The contributor reports the lesion is flat · close-up view · reported lesion symptoms include bothersome appearance · no relevant systemic symptoms · the contributor reports the condition has been present for one to three months · the affected area is the top or side of the foot and leg · the patient is 18–29, male — 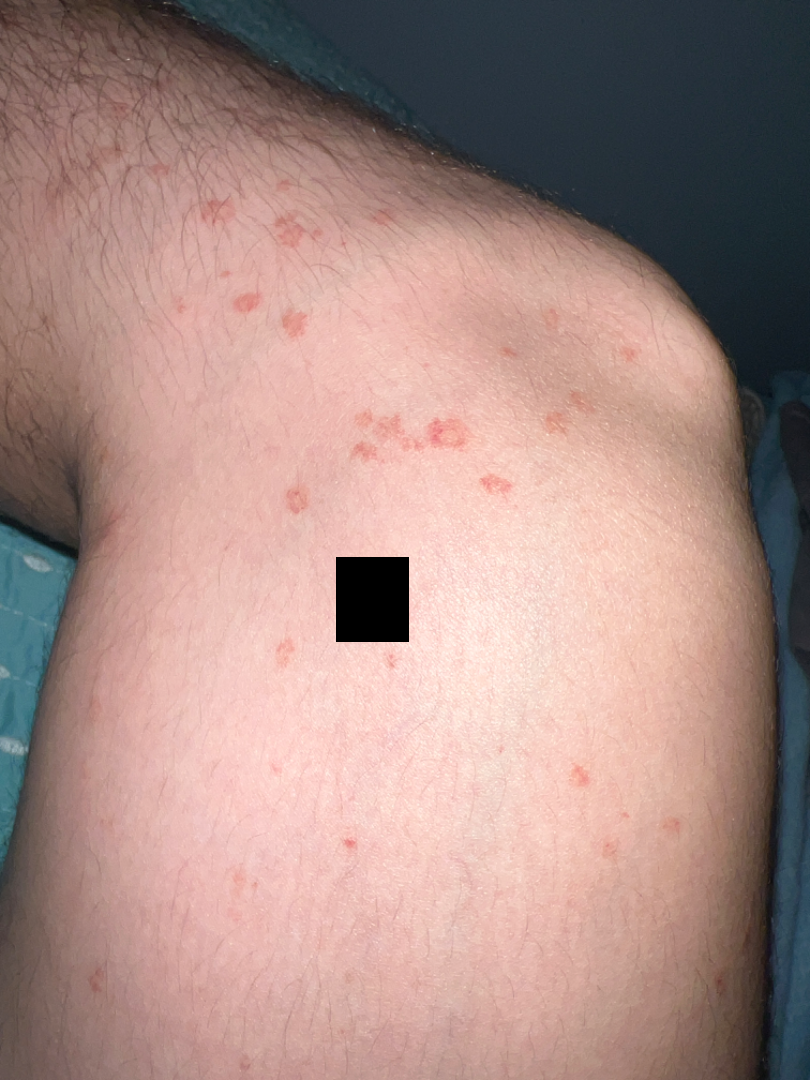Case summary:
* dermatologist impression: favoring Pigmented purpuric eruption; with consideration of Tinea; possibly Eczema